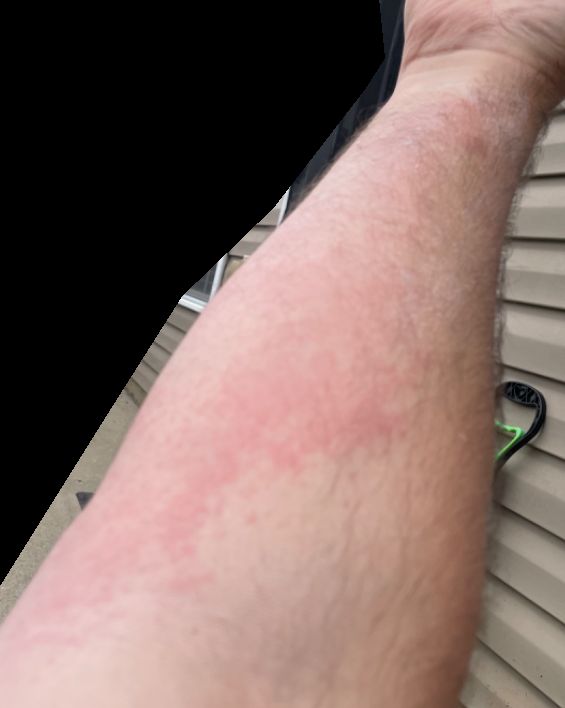Findings:
The case was indeterminate on photographic review.